The patient is a female roughly 45 years of age; a skin lesion imaged with a dermatoscope — 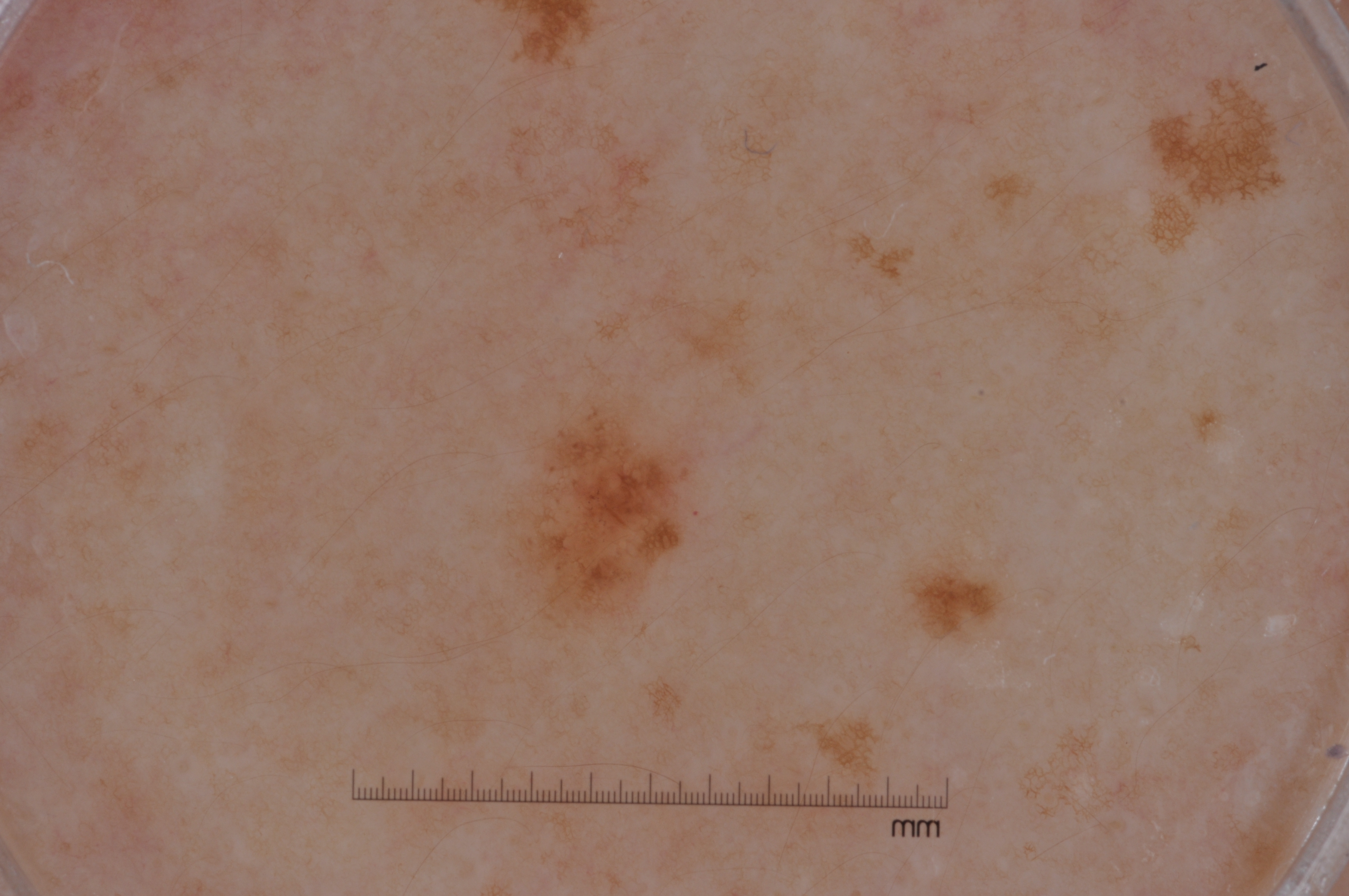The lesion occupies roughly 3% of the field. On dermoscopy, the lesion shows pigment network. In (x1, y1, x2, y2) order, lesion location: box(491, 352, 699, 643). Diagnosed as a melanocytic nevus.